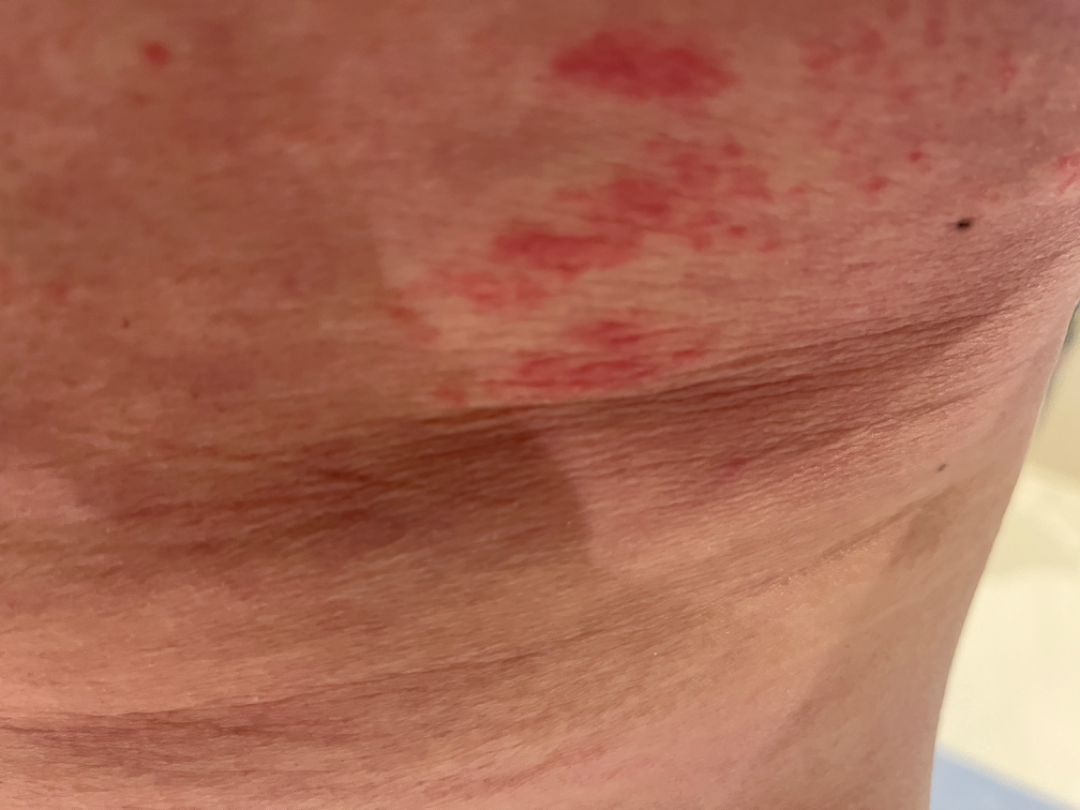Q: Could the case be diagnosed?
A: could not be assessed
Q: Where on the body?
A: back of the torso and front of the torso
Q: How long has this been present?
A: less than one week
Q: Who is the patient?
A: male, age 60–69
Q: Texture?
A: raised or bumpy
Q: What is the framing?
A: close-up